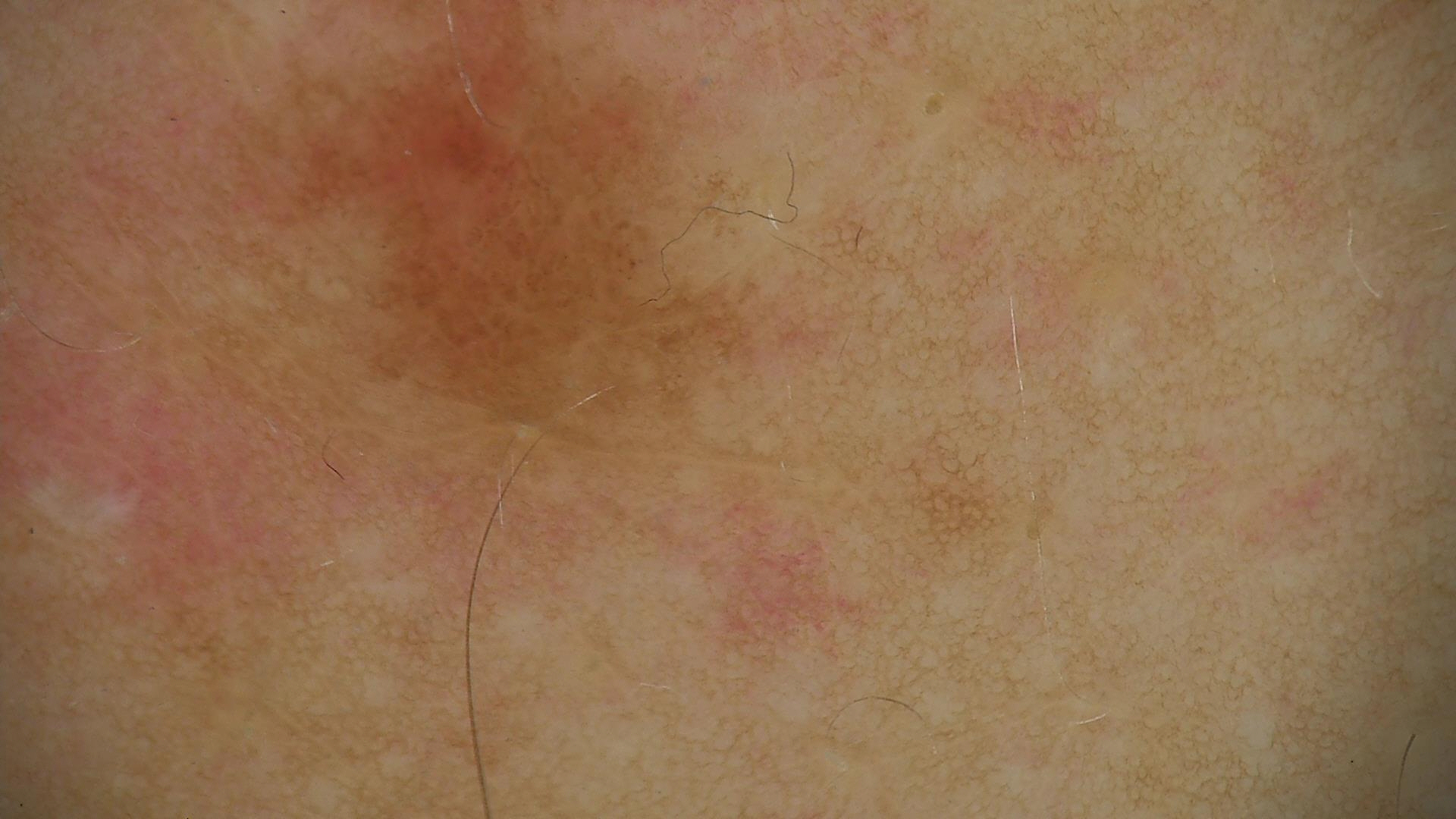Labeled as a solar lentigo.